The photograph is a close-up of the affected area · the contributor reports pain, burning and itching · the patient is a female aged 50–59 · the lesion is described as raised or bumpy · located on the front of the torso · the patient considered this a rash · associated systemic symptoms include joint pain · the contributor reports the condition has been present for less than one week.
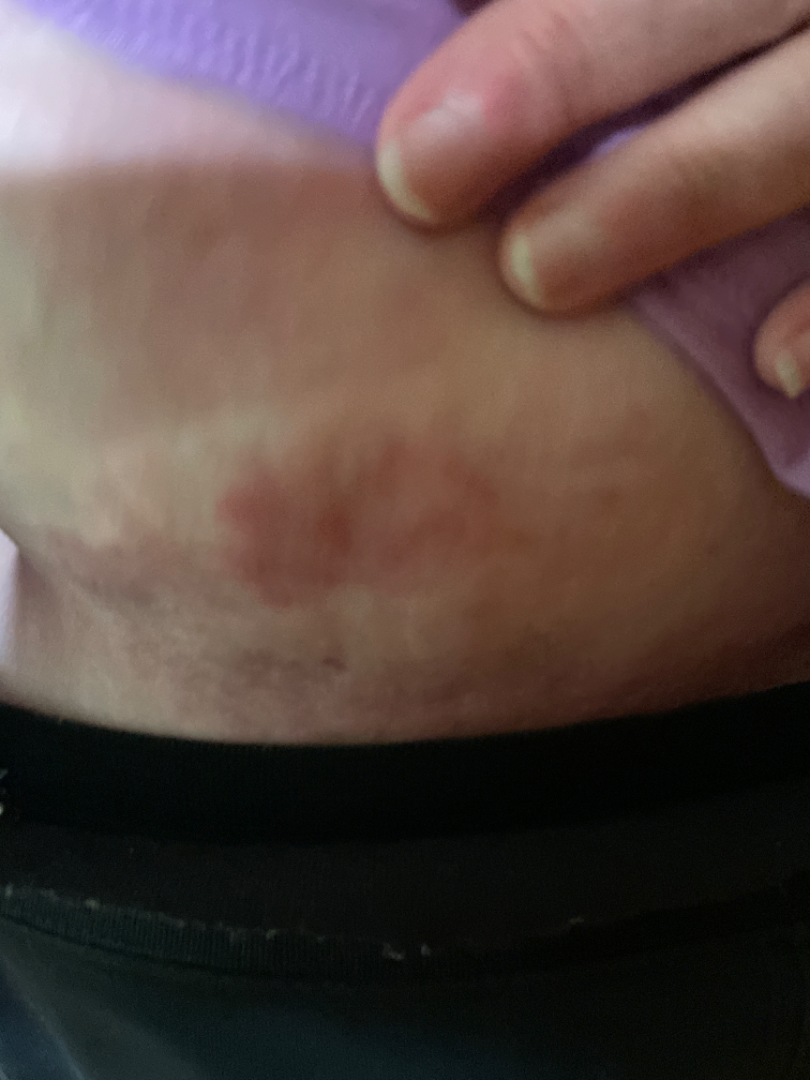  assessment: unable to determine